The photograph is a close-up of the affected area: 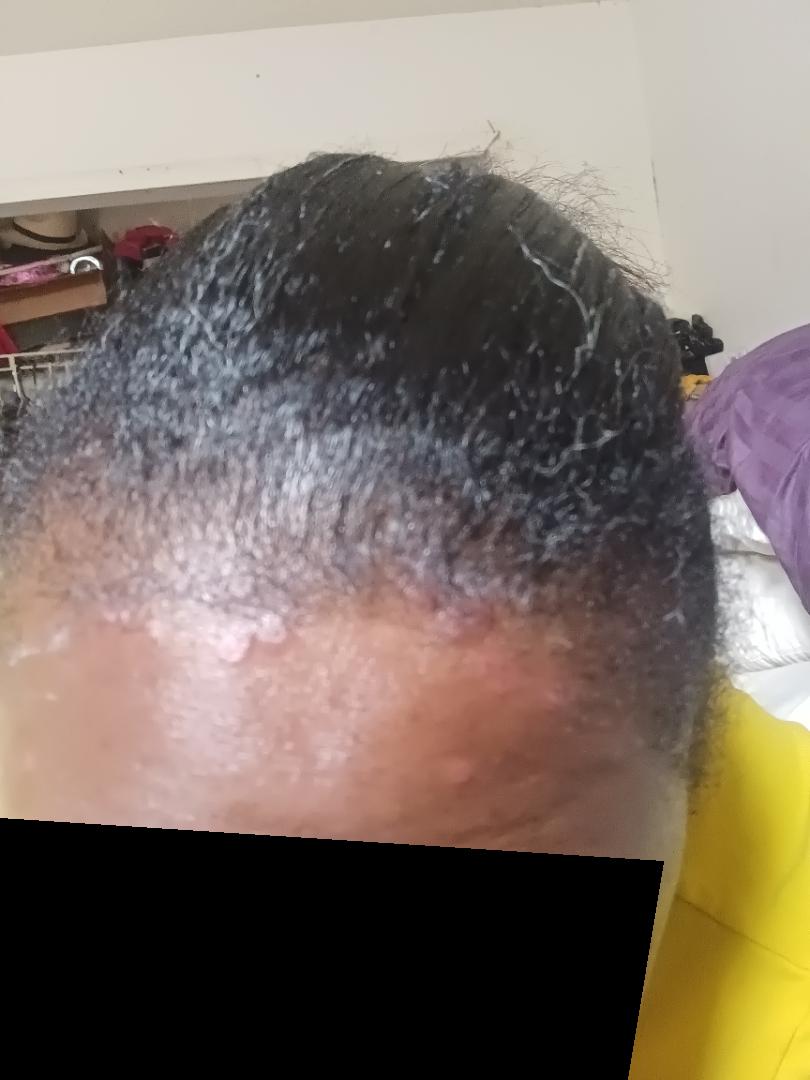No differential diagnosis could be assigned on photographic review.